A female subject 78 years of age · a dermoscopic image of a skin lesion · imaged for a research study, with no referral diagnosis recorded:
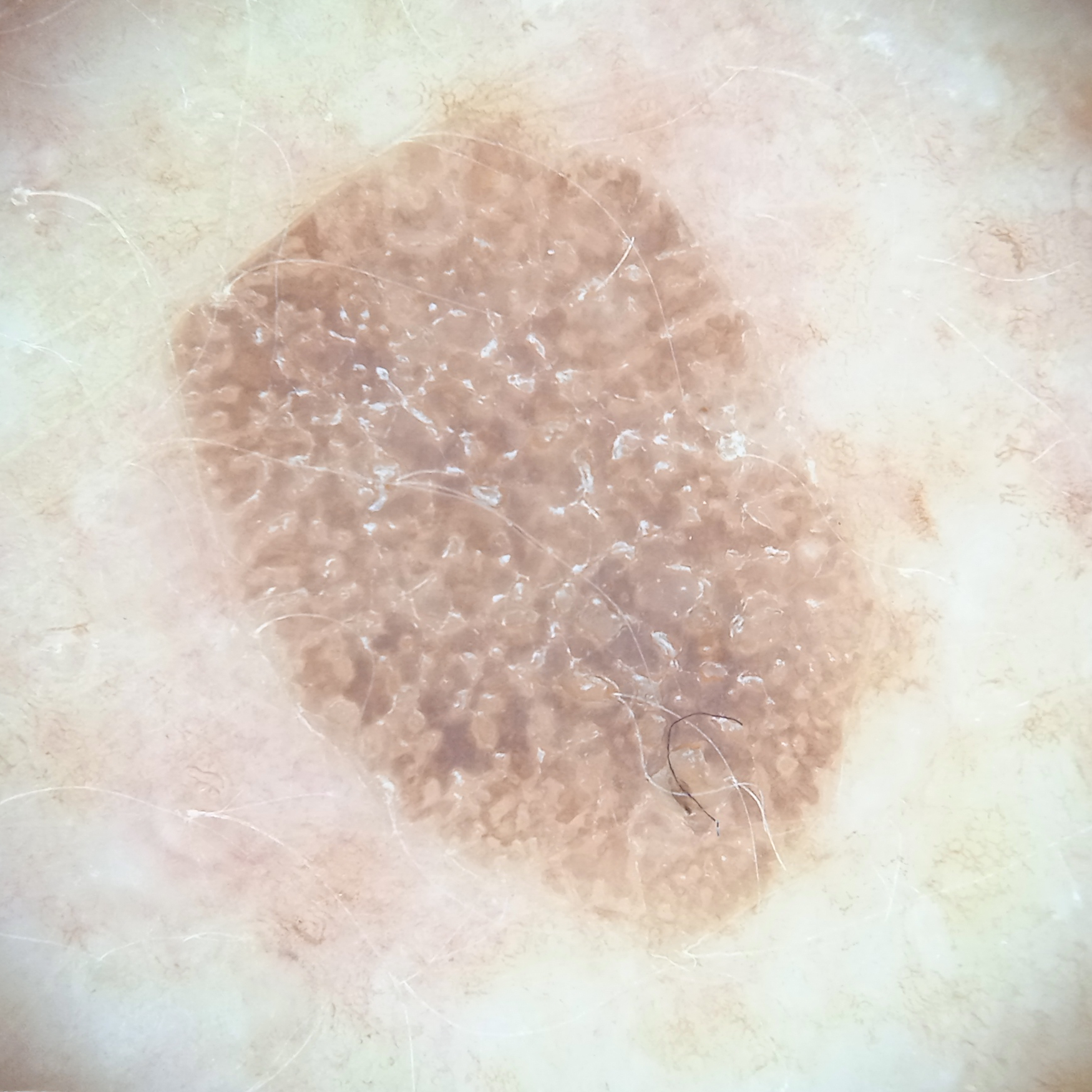The lesion involves the back. The lesion measures approximately 9.6 mm. The dermatologists' assessment was a seborrheic keratosis.